Imaged for a research study, with no referral diagnosis recorded; a macroscopic clinical photograph of a skin lesion; a female subject 60 years of age:
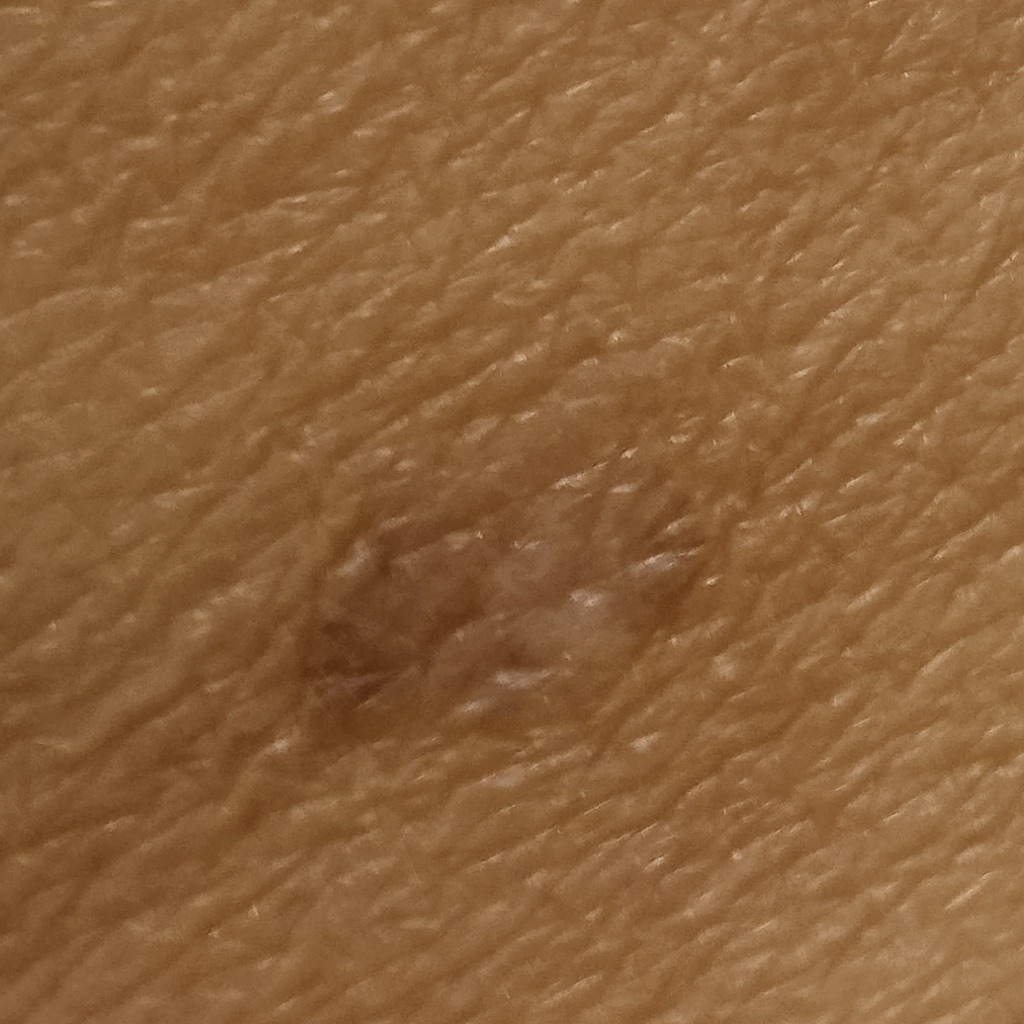Findings: Located on the torso. Conclusion: The dermatologists' assessment was a melanocytic nevus.